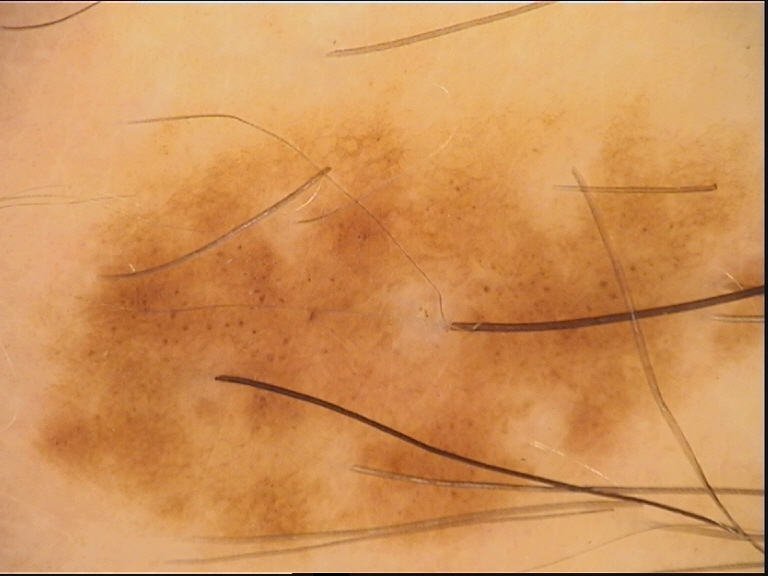Impression: Labeled as a benign lesion — a dysplastic compound nevus.